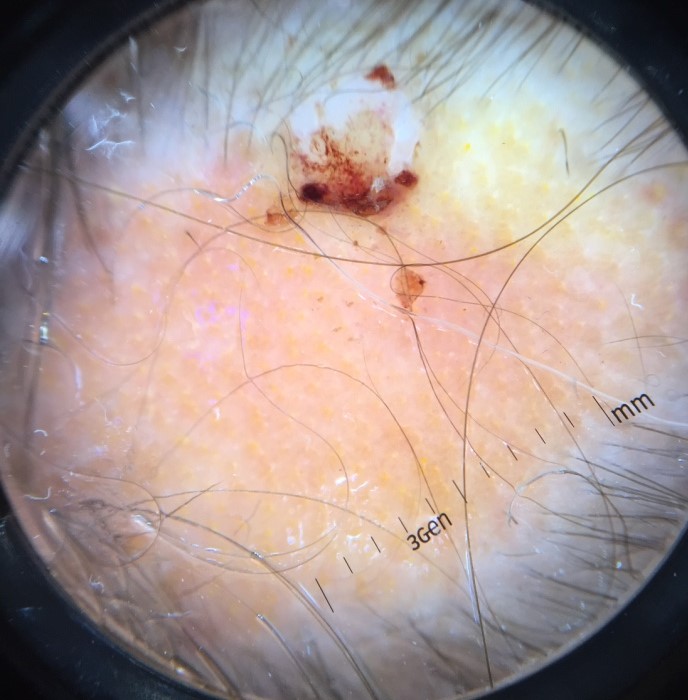Dermoscopy of a skin lesion. The biopsy diagnosis was a keratinocytic, malignant lesion — a squamous cell carcinoma.